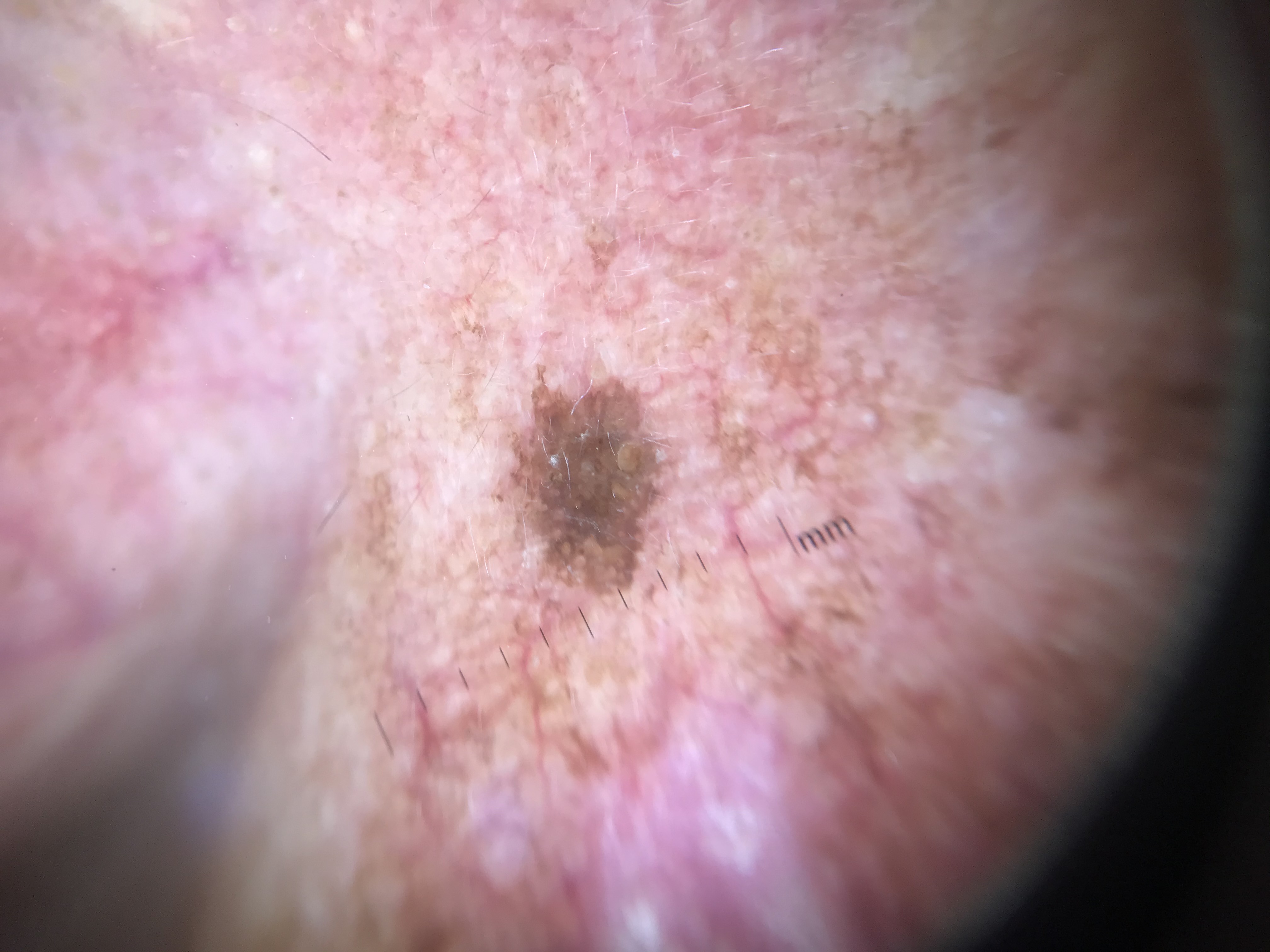lesion type: keratinocytic; label: seborrheic keratosis (expert consensus).